A dermoscopy image of a single skin lesion: 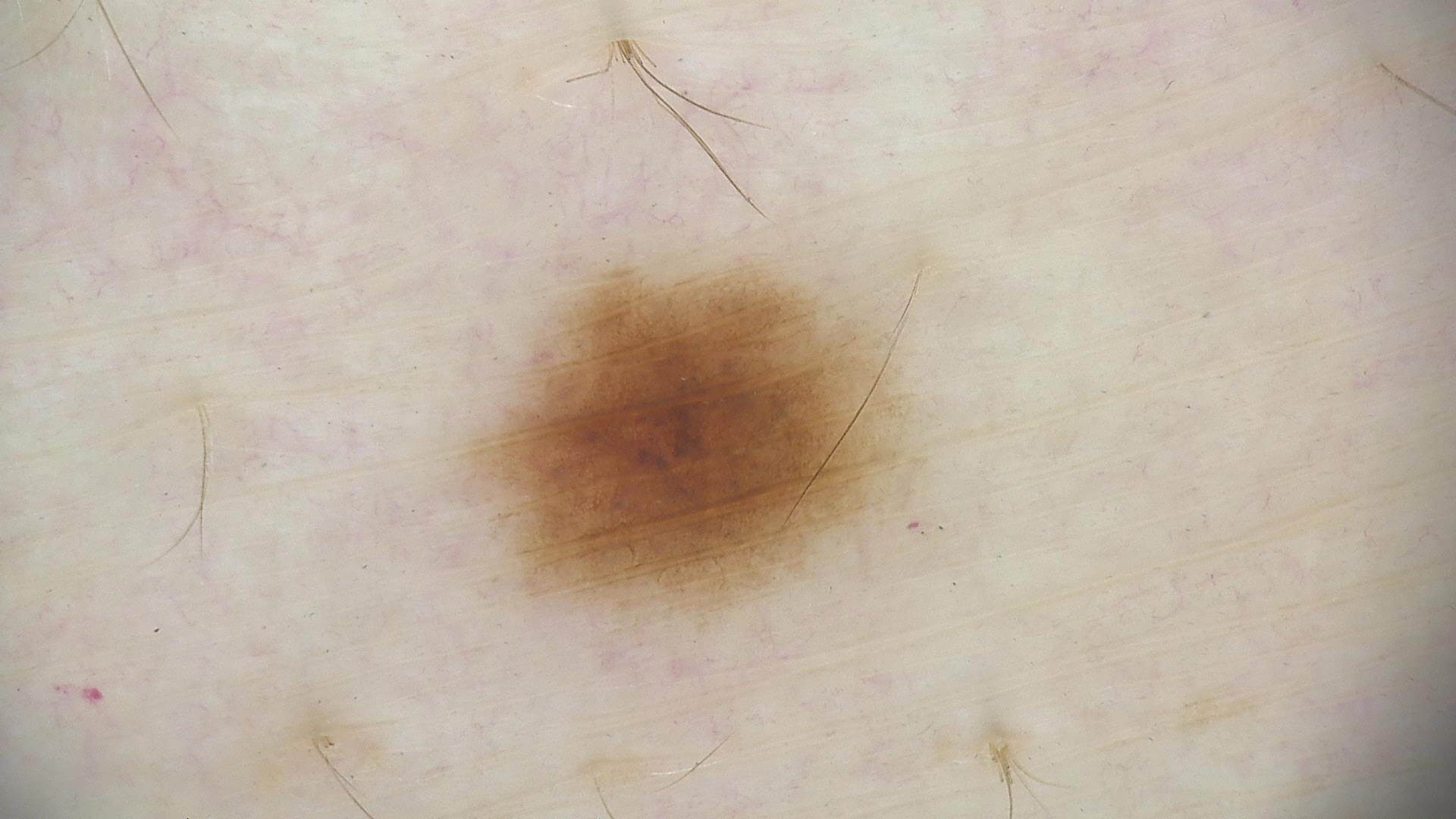{
  "diagnosis": {
    "name": "dysplastic junctional nevus",
    "code": "jd",
    "malignancy": "benign",
    "super_class": "melanocytic",
    "confirmation": "expert consensus"
  }
}